A dermatoscopic image of a skin lesion.
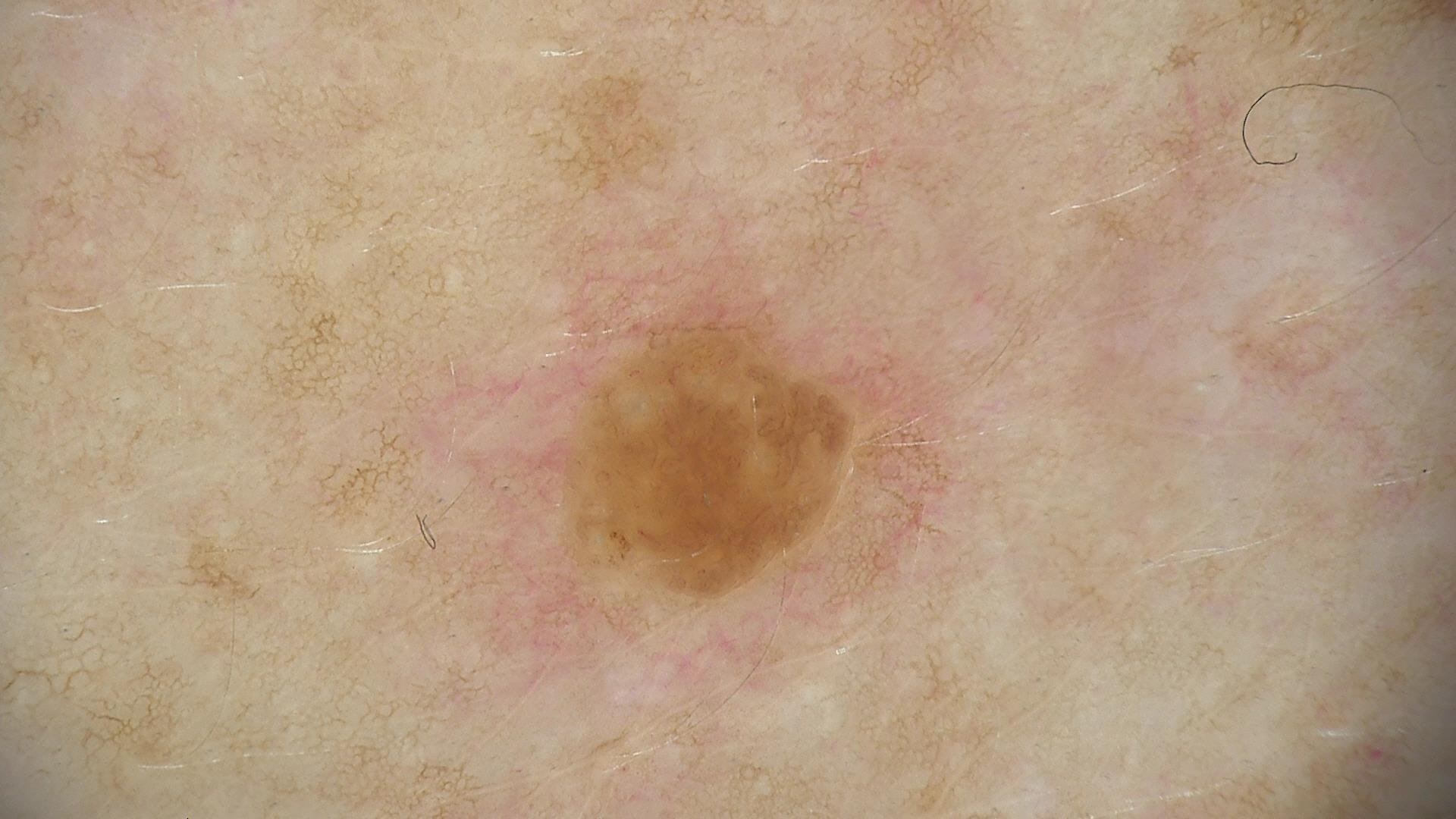Q: What kind of lesion is this?
A: banal
Q: What is this lesion?
A: dermal nevus (expert consensus)